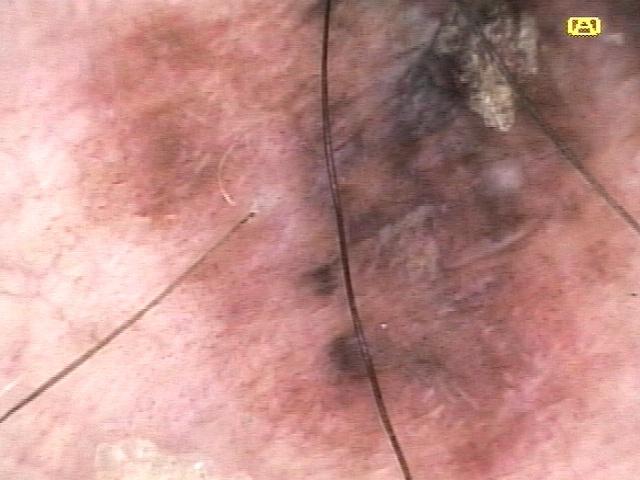Contact-polarized dermoscopy of a skin lesion. A male patient in their mid- to late 80s or older. The lesion is located on a lower extremity. Histopathologically confirmed as a melanoma.